A dermoscopy image of a single skin lesion.
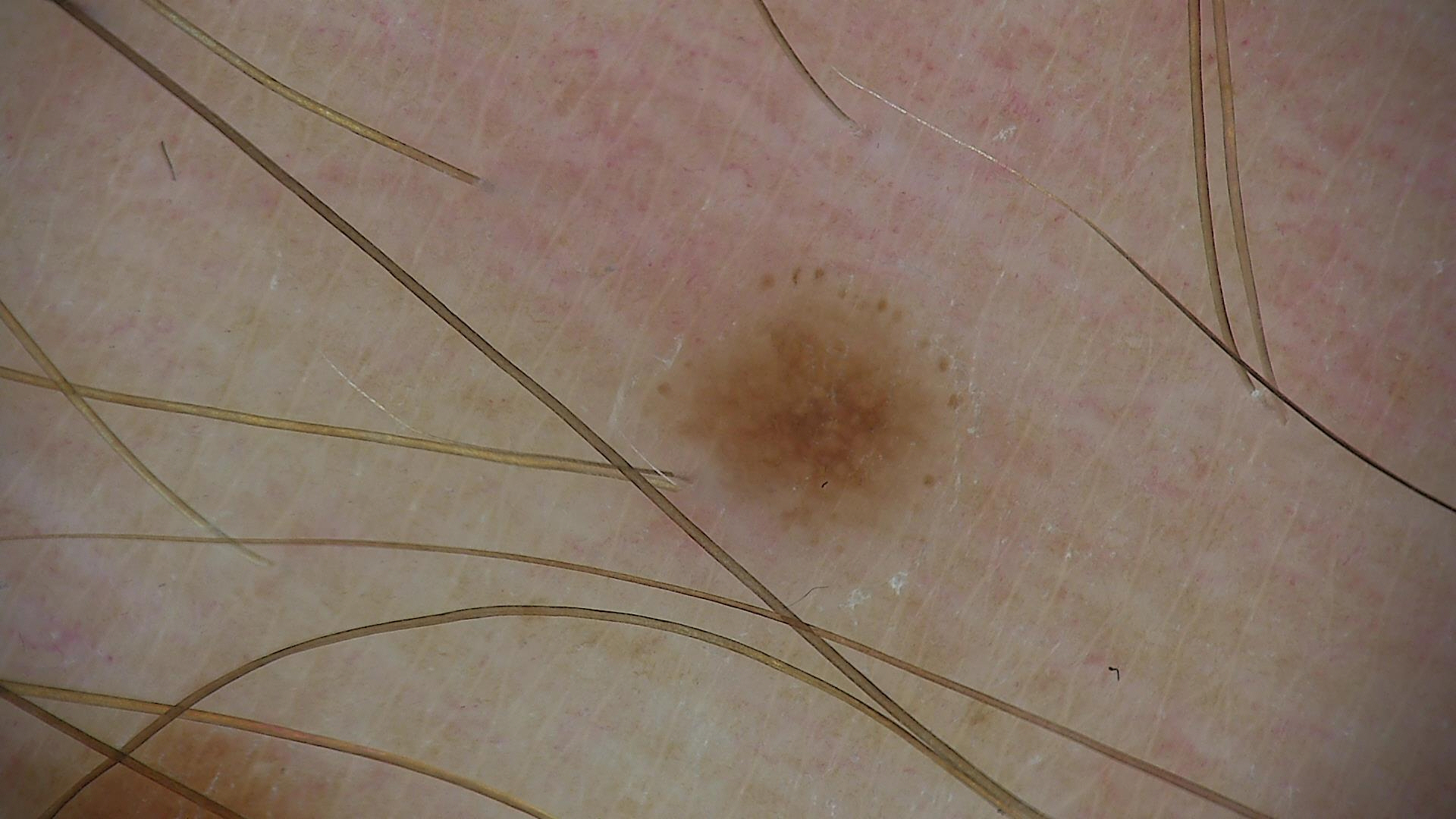diagnostic label = dysplastic junctional nevus (expert consensus)